The photograph is a close-up of the affected area.
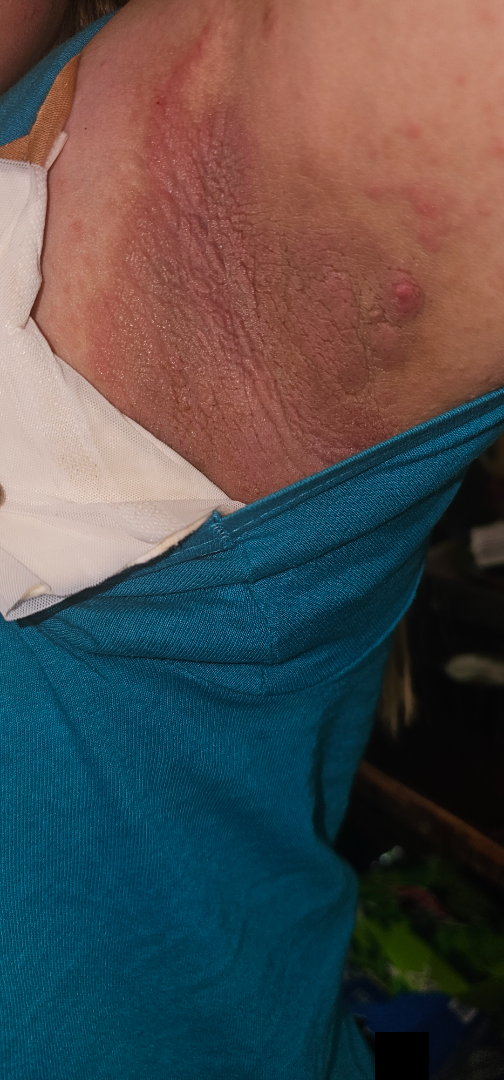<summary>
  <differential>
    <tied_lead>Intertrigo, Eczema</tied_lead>
    <unlikely>Psoriasis</unlikely>
  </differential>
</summary>